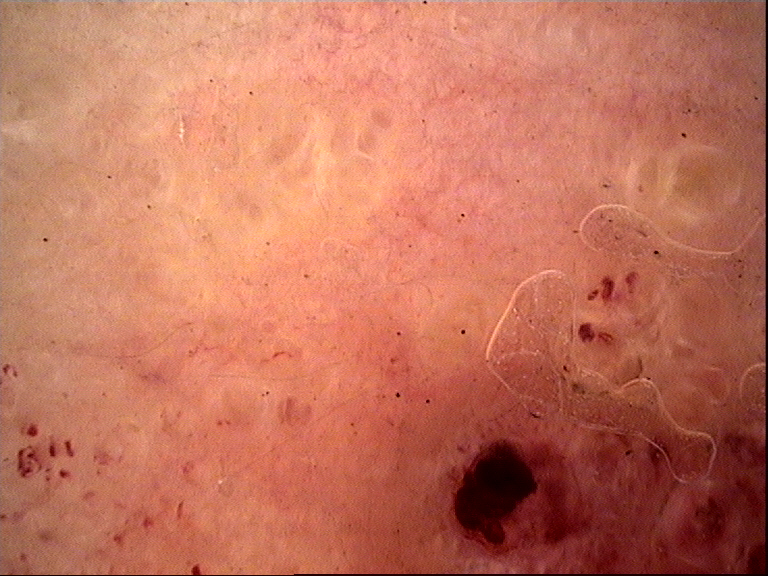A dermatoscopic image of a skin lesion.
The morphology is that of a vascular lesion.
Labeled as a lymphangioma.